The chart records a previous melanoma.
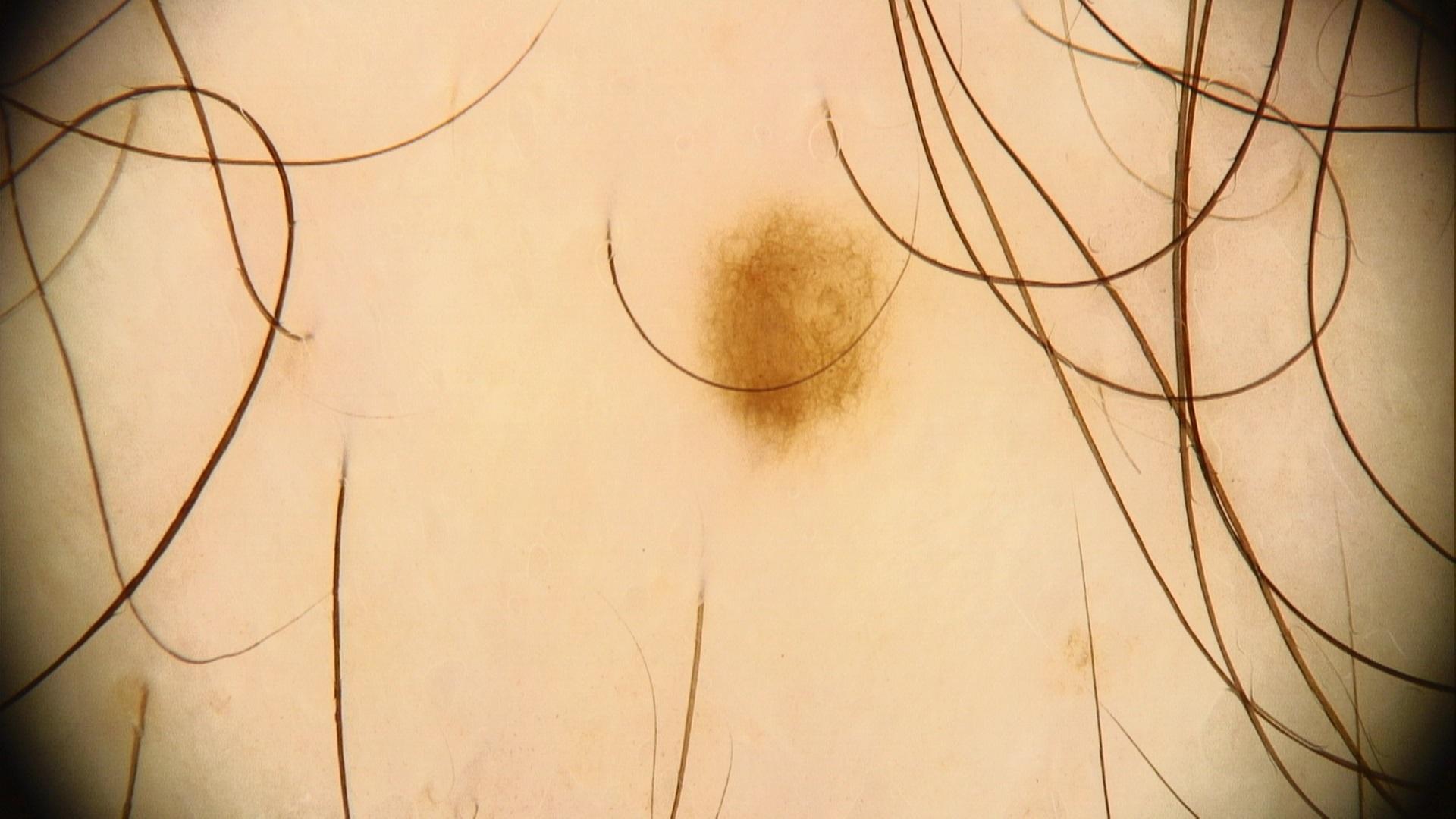anatomic site — the trunk | impression — Nevus.